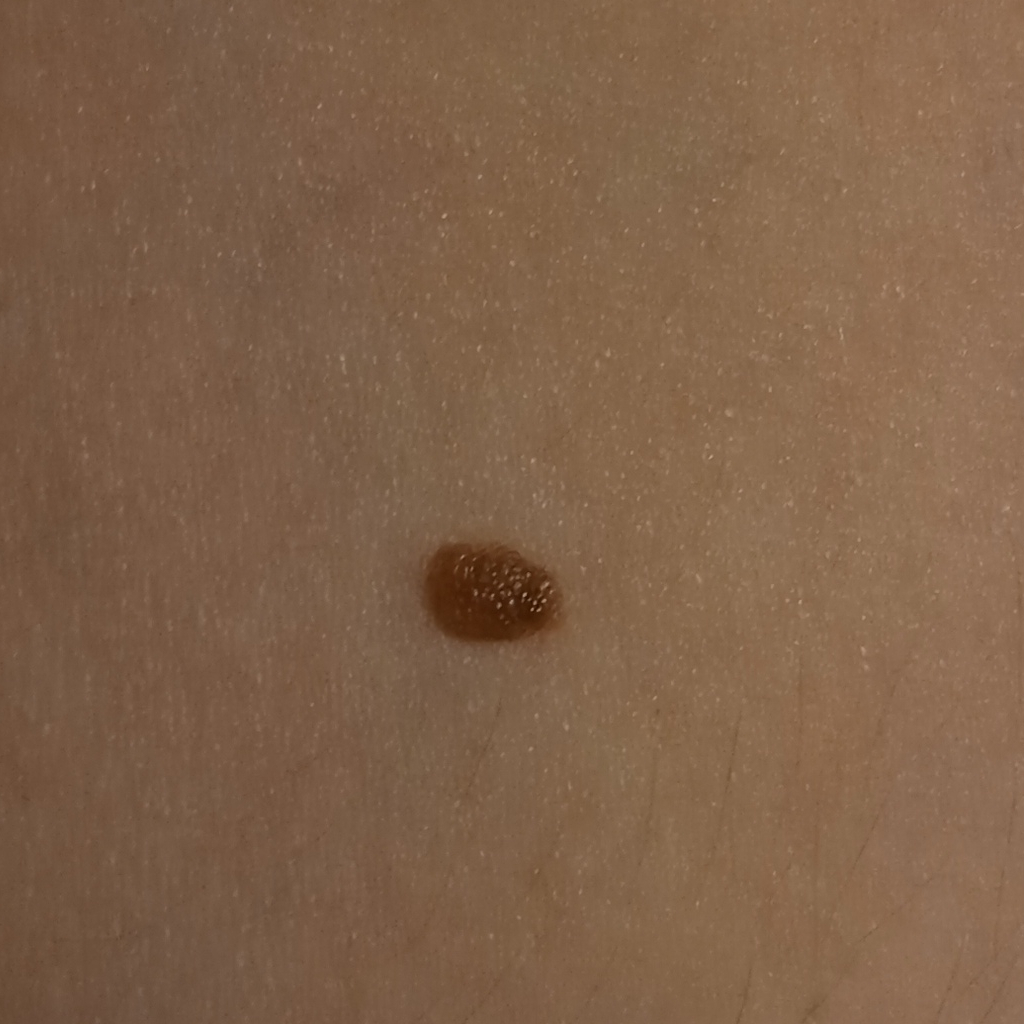subject: female, 26 years old; referral: research study (no referral diagnosis); image: clinical photo; anatomic site: an arm; diameter: 5.5 mm; assessment: melanocytic nevus (dermatologist consensus).